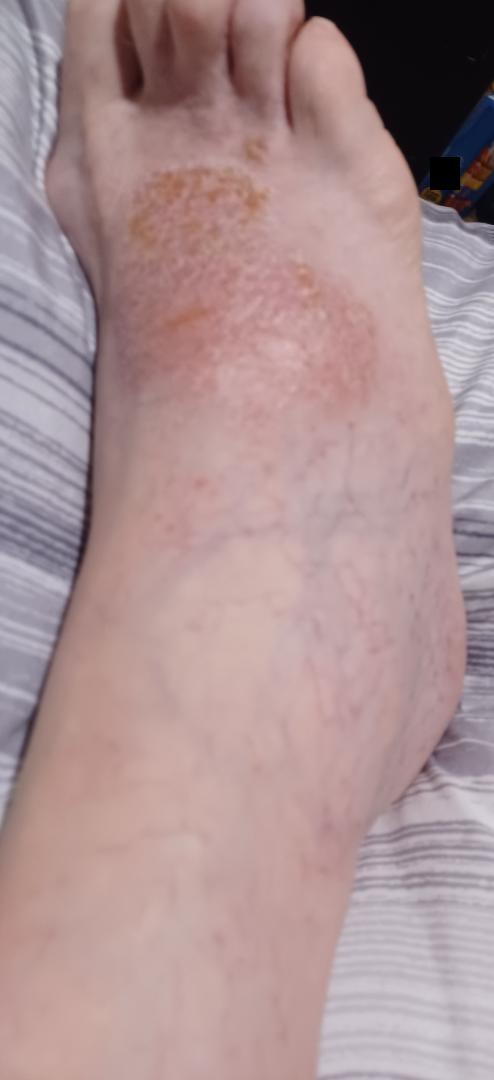dermatologist impression = a single dermatologist reviewed the case: most likely Allergic Contact Dermatitis; possibly Impetigo; an alternative is Irritant Contact Dermatitis.